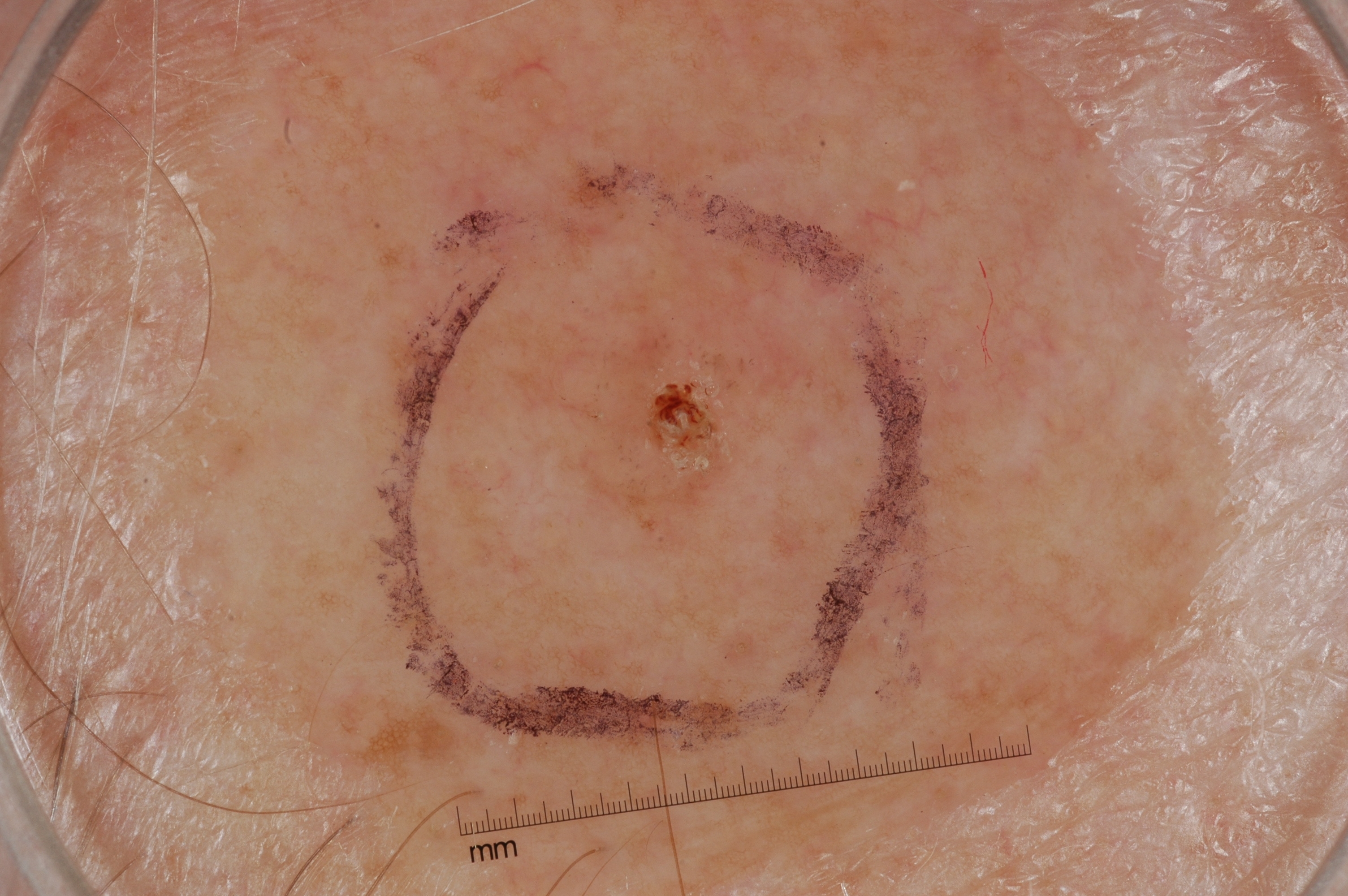Image and clinical context: This is a dermoscopic photograph of a skin lesion. The patient is a male aged approximately 60. In (x1, y1, x2, y2) order, the lesion is bounded by 538 299 784 506. Dermoscopic assessment notes no pigment network, milia-like cysts, streaks, or negative network. Conclusion: The lesion was assessed as a seborrheic keratosis.